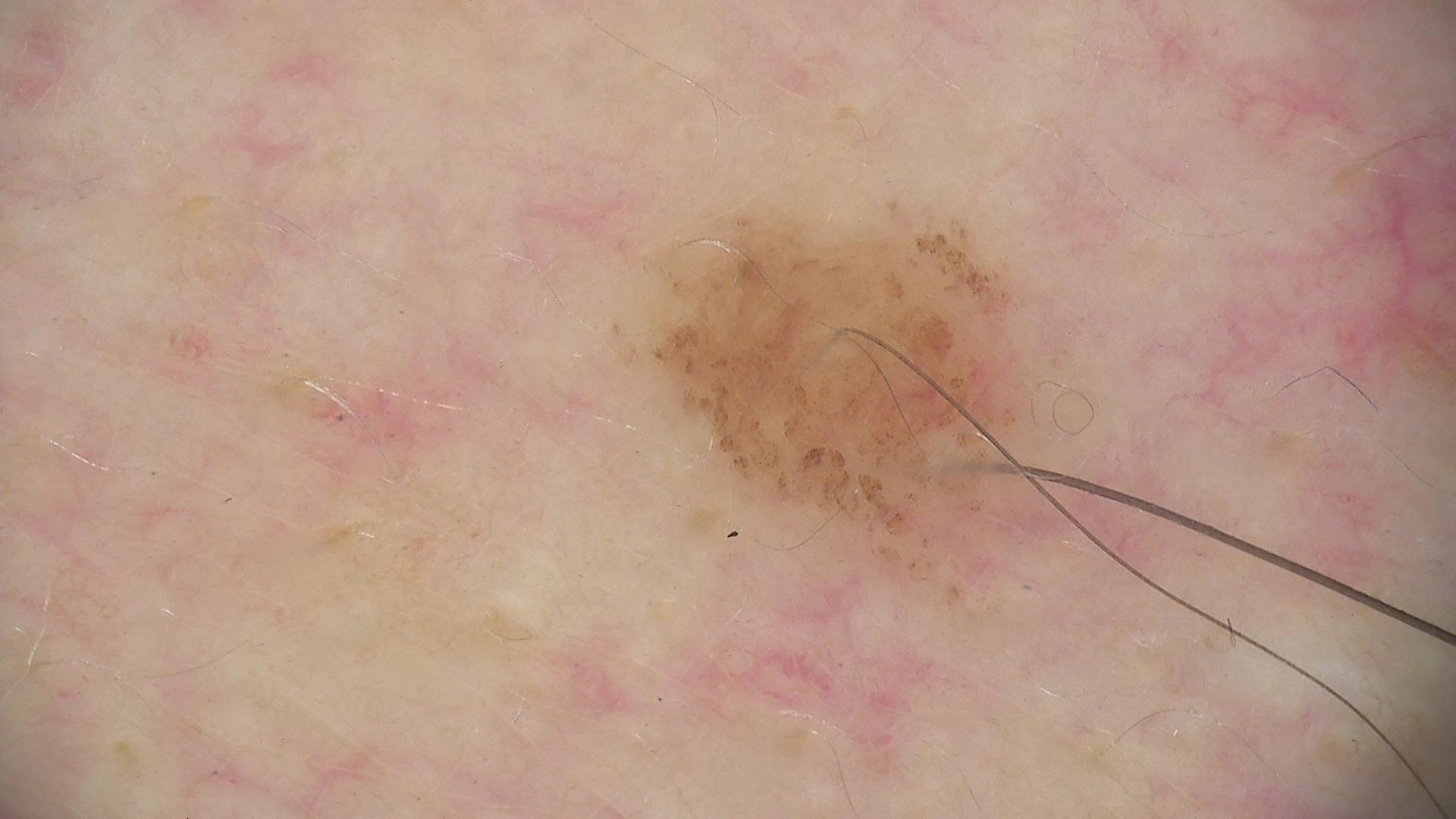assessment=dysplastic junctional nevus (expert consensus).